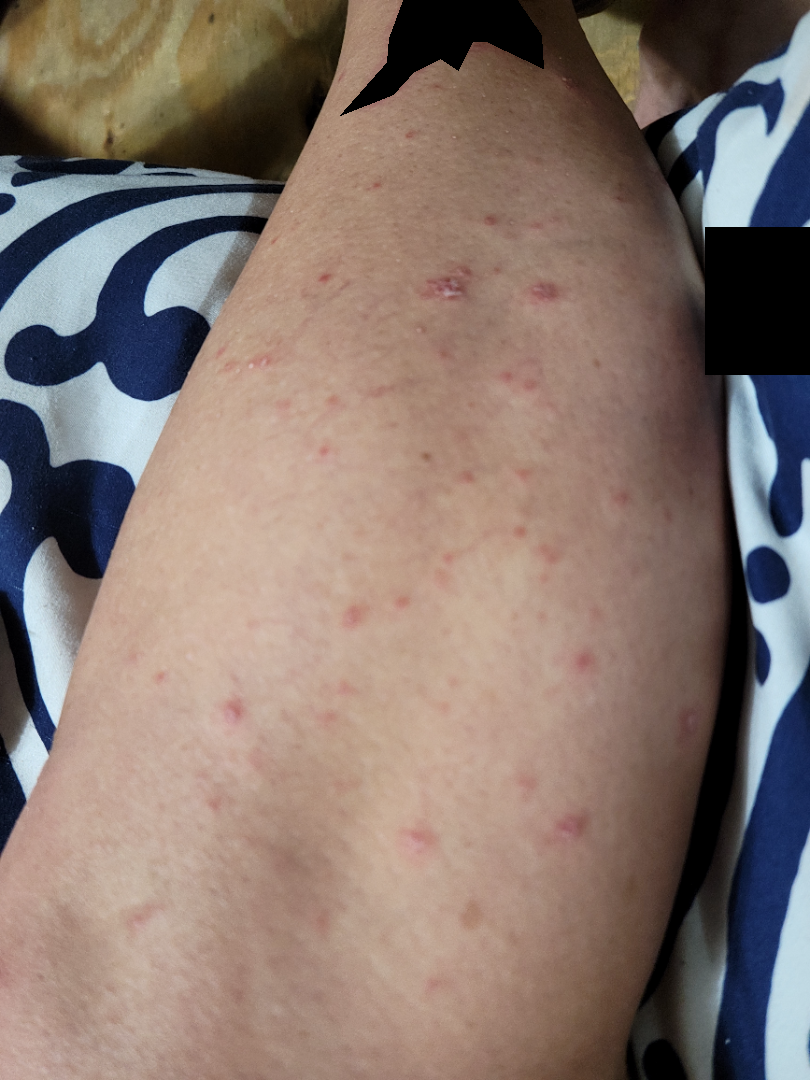History:
The photograph is a close-up of the affected area. The contributor is a female aged 30–39. The leg, top or side of the foot, arm and front of the torso are involved.
Impression:
The reviewing panel's impression was: most consistent with Psoriasis; an alternative is Lichen planus/lichenoid eruption; less likely is Scabies; less probable is Lymphomatoid papulosis; a remote consideration is Pityriasis lichenoides.